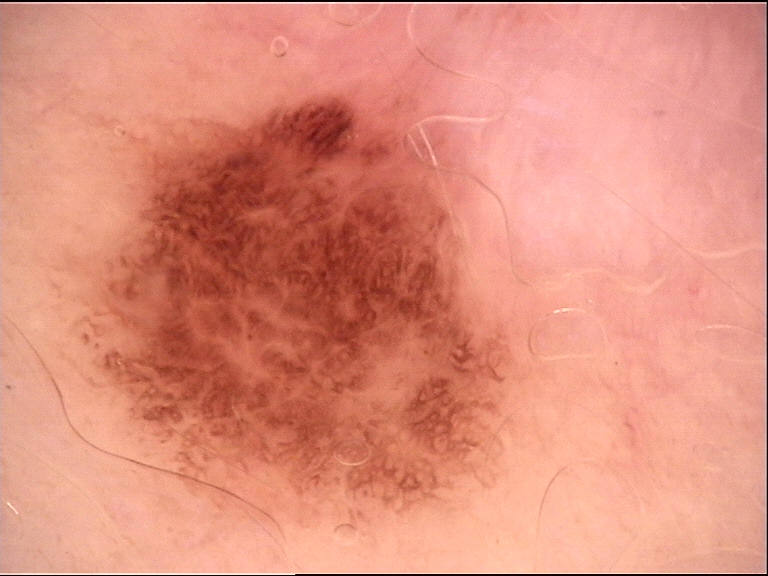Impression:
Consistent with a dysplastic junctional nevus.